The subject is 50–59, male. The top or side of the foot is involved. Present for more than five years. The patient described the issue as a nail problem. This is a close-up image — 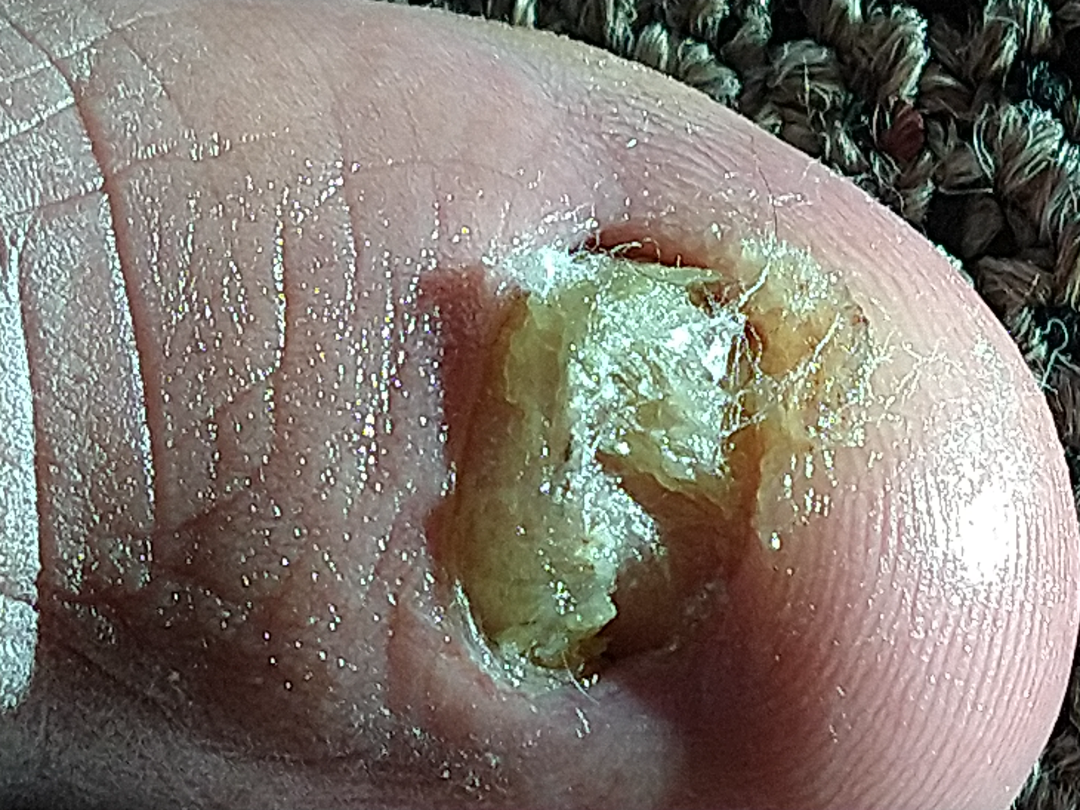The favored diagnosis is Onychomycosis.